A dermatoscopic image of a skin lesion: 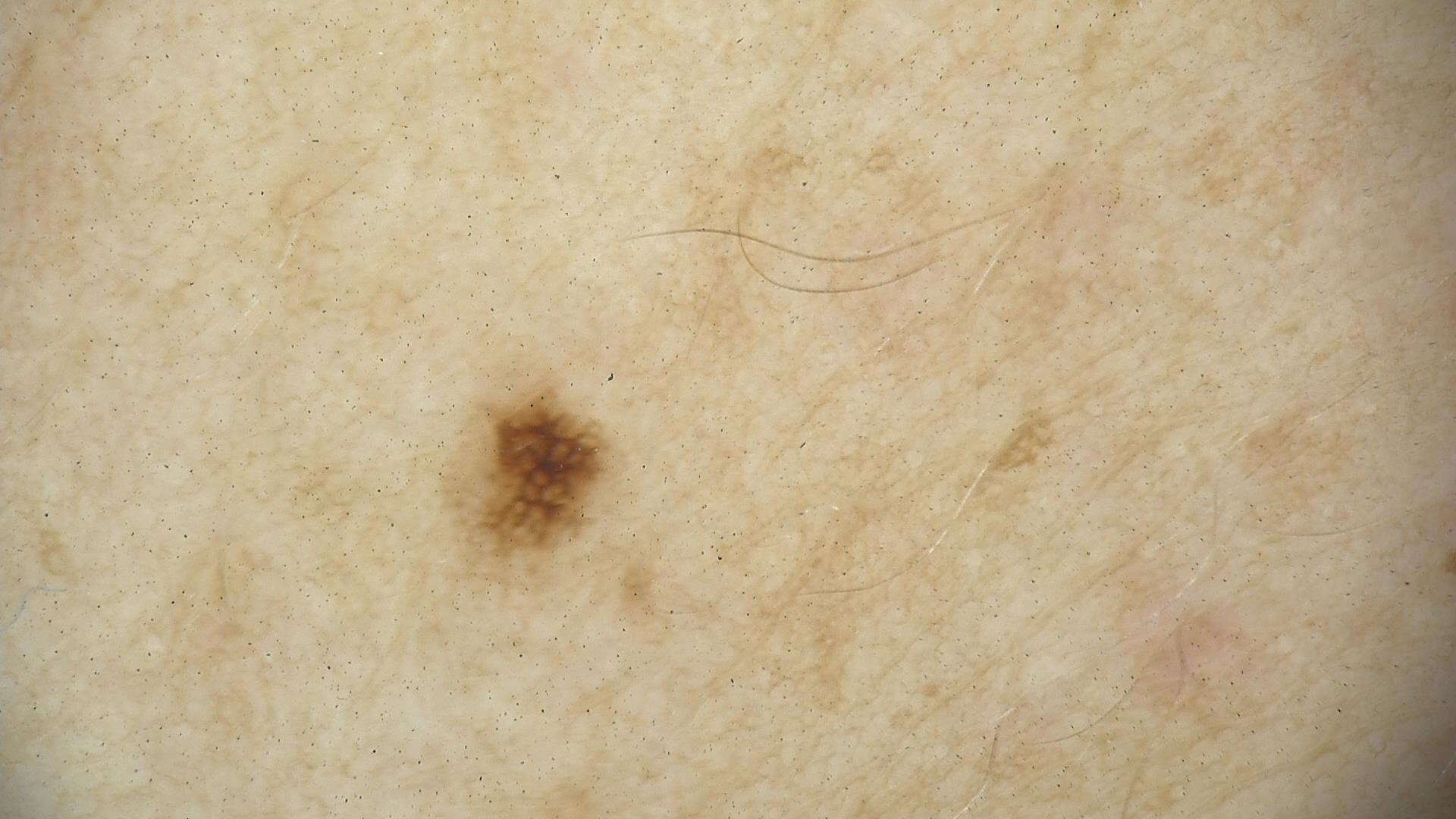Case:
* diagnostic label: dysplastic junctional nevus (expert consensus)